A skin lesion imaged with a dermatoscope: 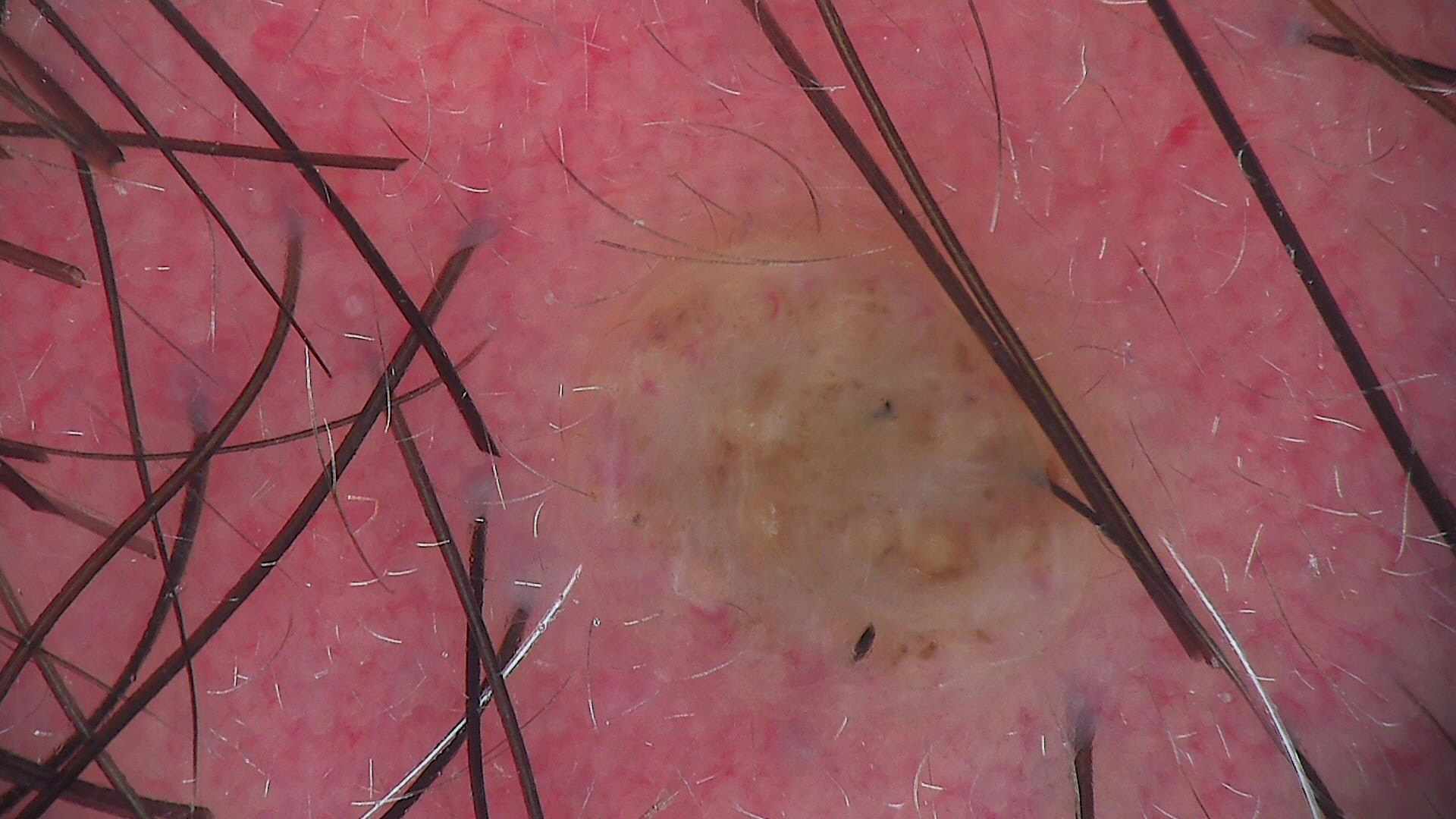The diagnostic label was a banal lesion — a dermal nevus.